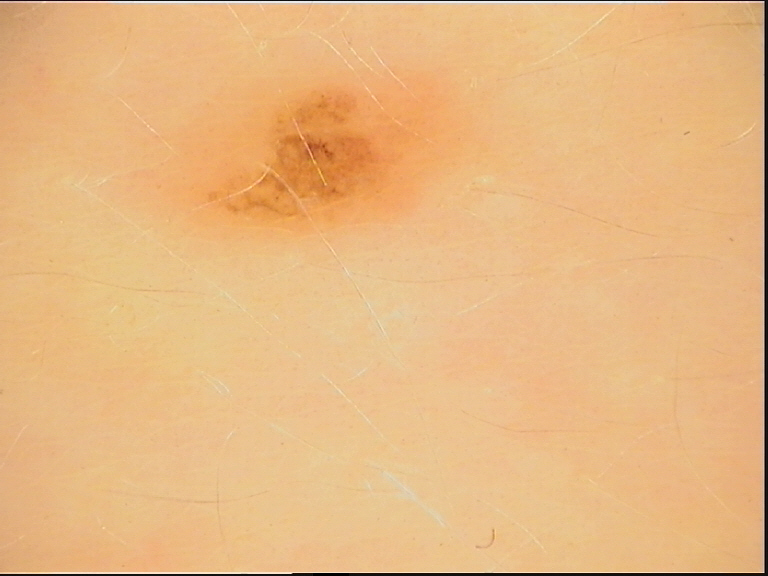<case>
<diagnosis>
<name>dysplastic junctional nevus</name>
<code>jd</code>
<malignancy>benign</malignancy>
<super_class>melanocytic</super_class>
<confirmation>expert consensus</confirmation>
</diagnosis>
</case>